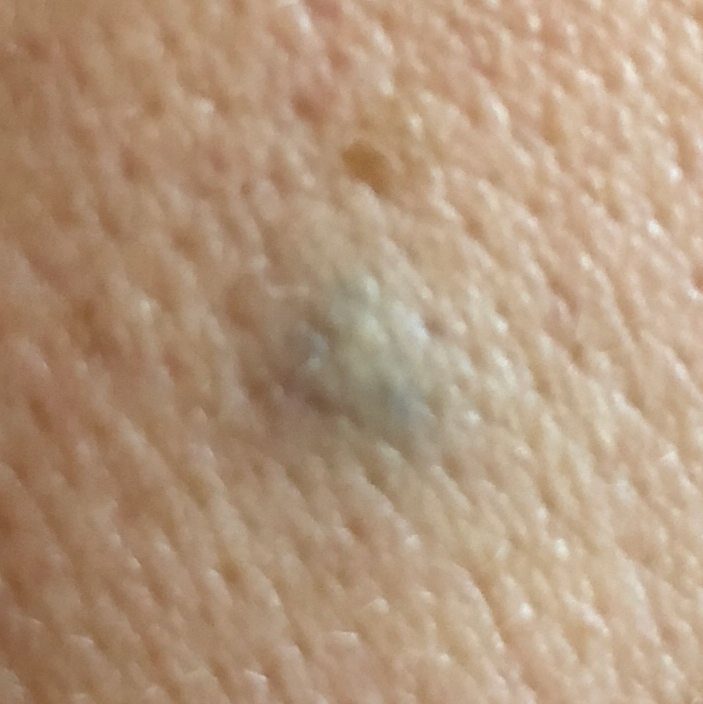subject = aged 43
image type = clinical photo
body site = the chest
diagnostic label = nevus (clinical consensus)